A dermoscopic close-up of a skin lesion.
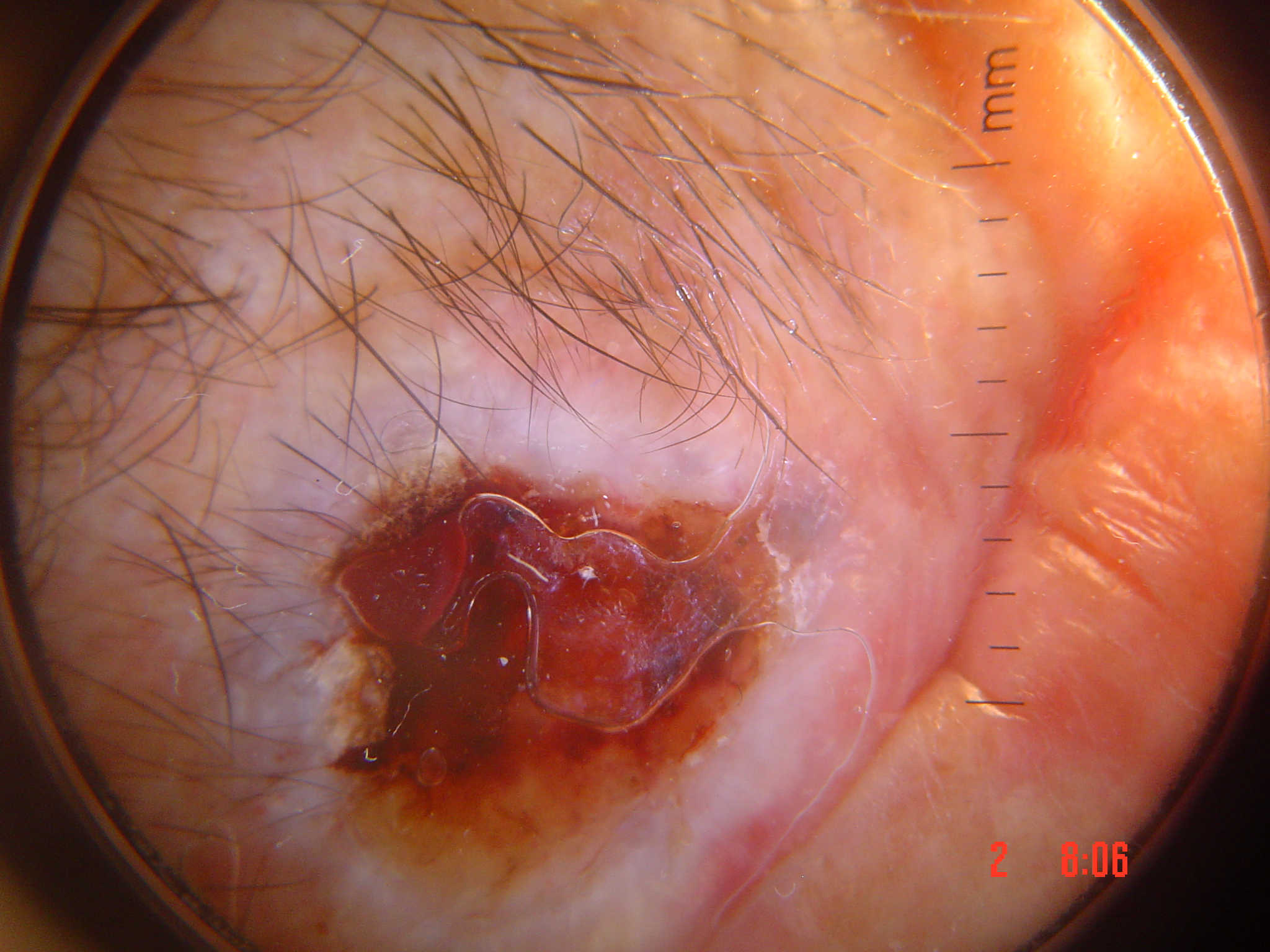Confirmed on histopathology as a malignant, keratinocytic lesion — a squamous cell carcinoma.